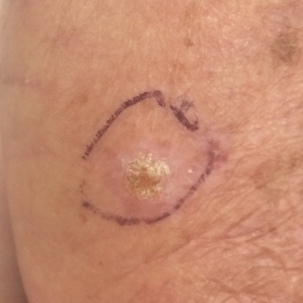Confirmed on histopathology as a squamous cell carcinoma.